A dermoscopy image of a single skin lesion.
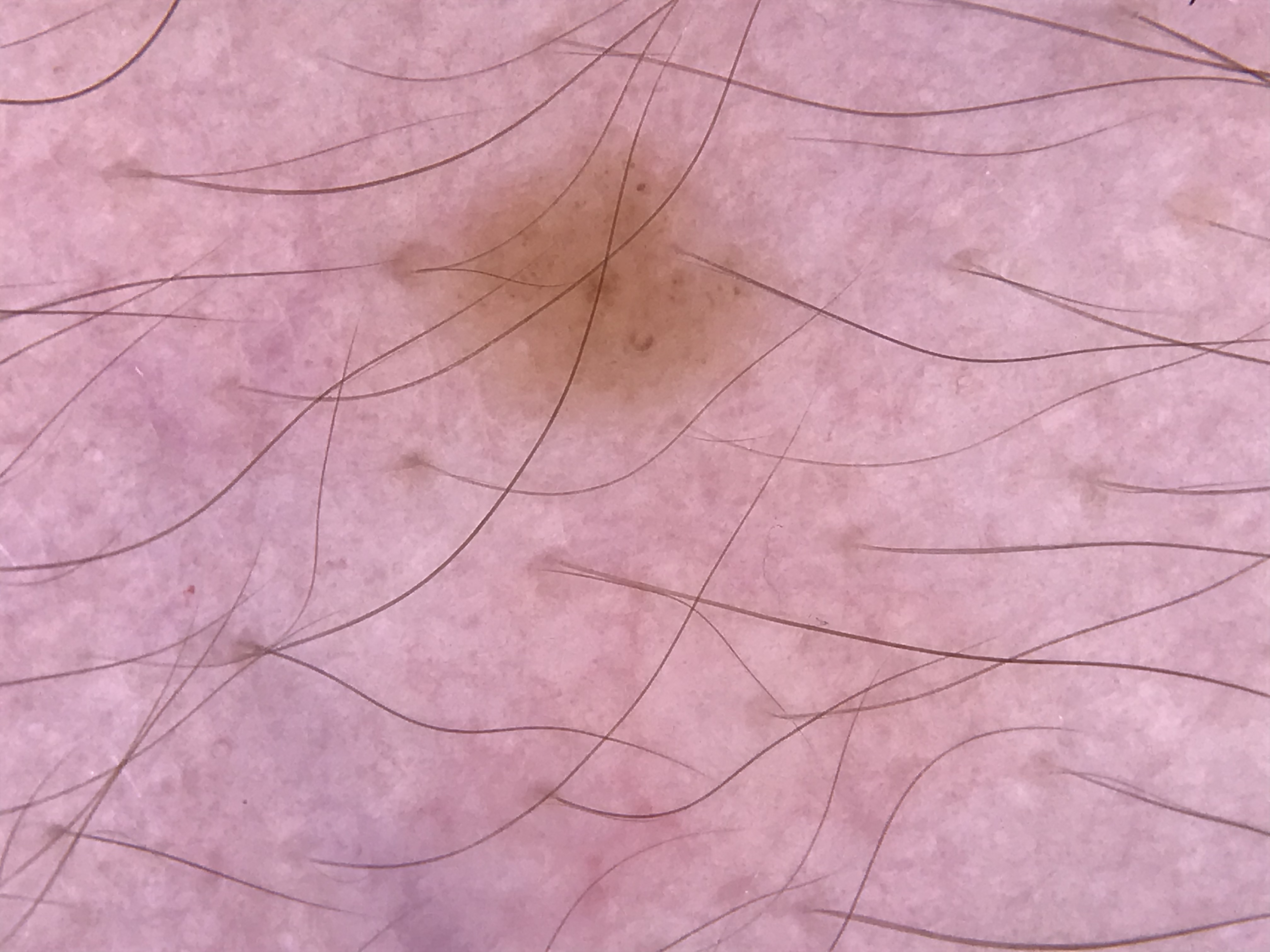This is a banal lesion. Classified as a junctional nevus.